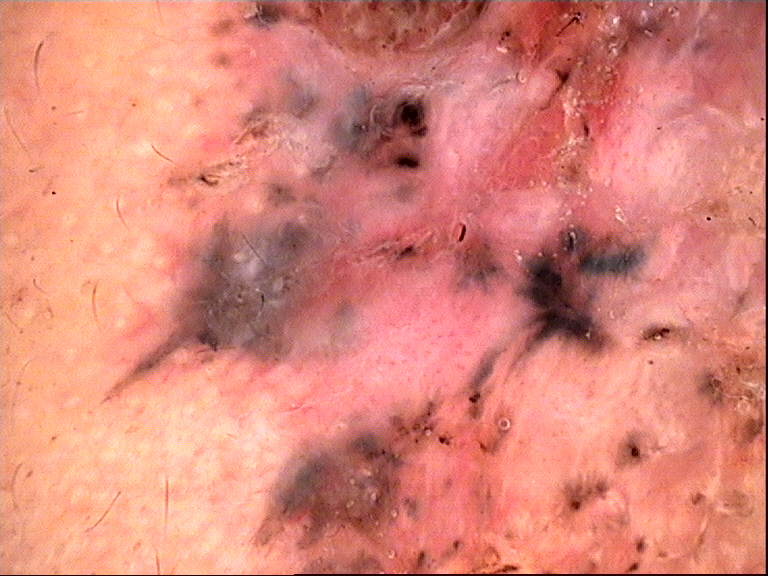diagnostic label: basal cell carcinoma (biopsy-proven).